A male subject 89 years old. A dermoscopic image of a skin lesion. The patient says their skin reddens painfully with sun exposure.
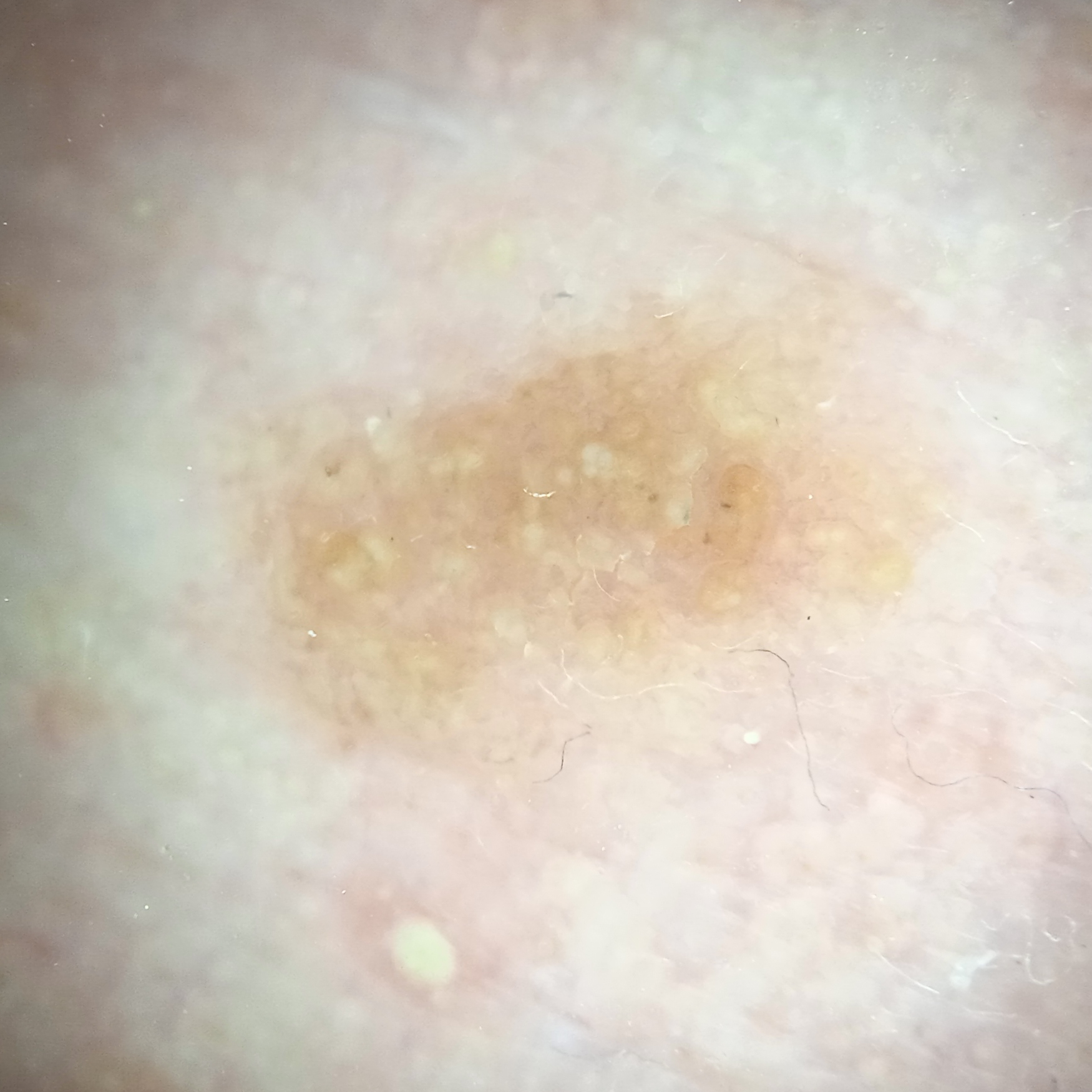The lesion measures approximately 6.4 mm.
The dermatologists' assessment was an actinic keratosis.